The photograph was taken at a distance; located on the leg: 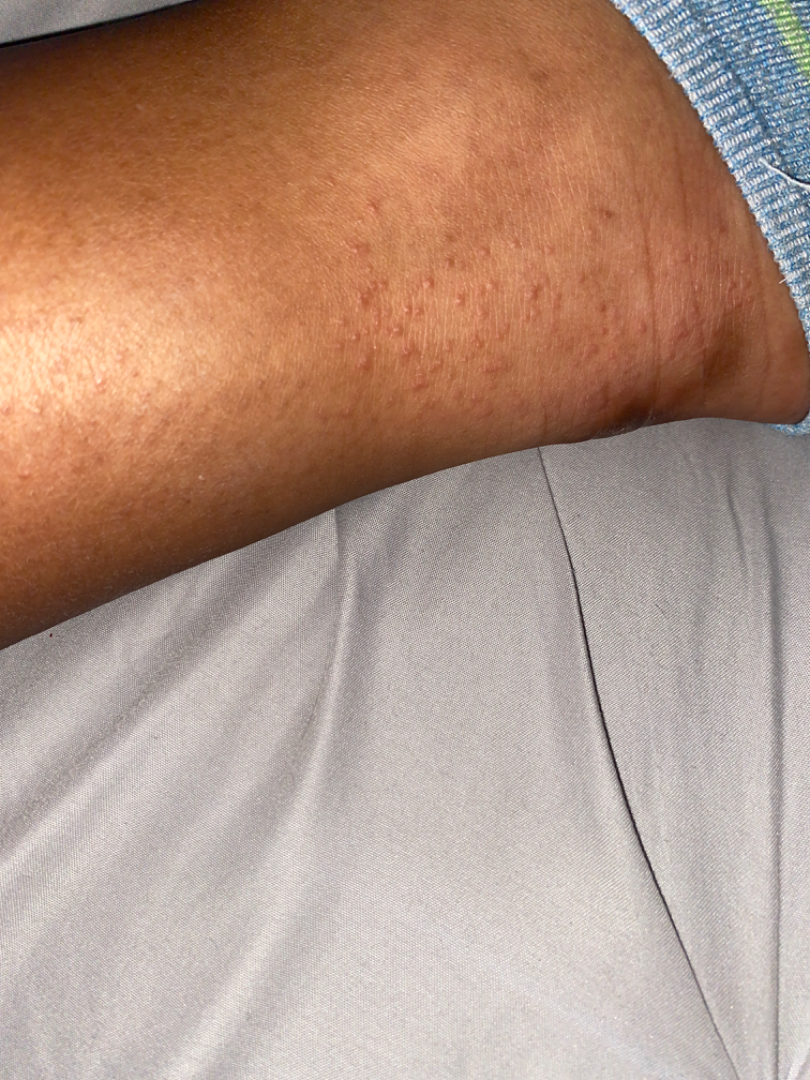Eczema (favored); Lichen planus/lichenoid eruption (considered).